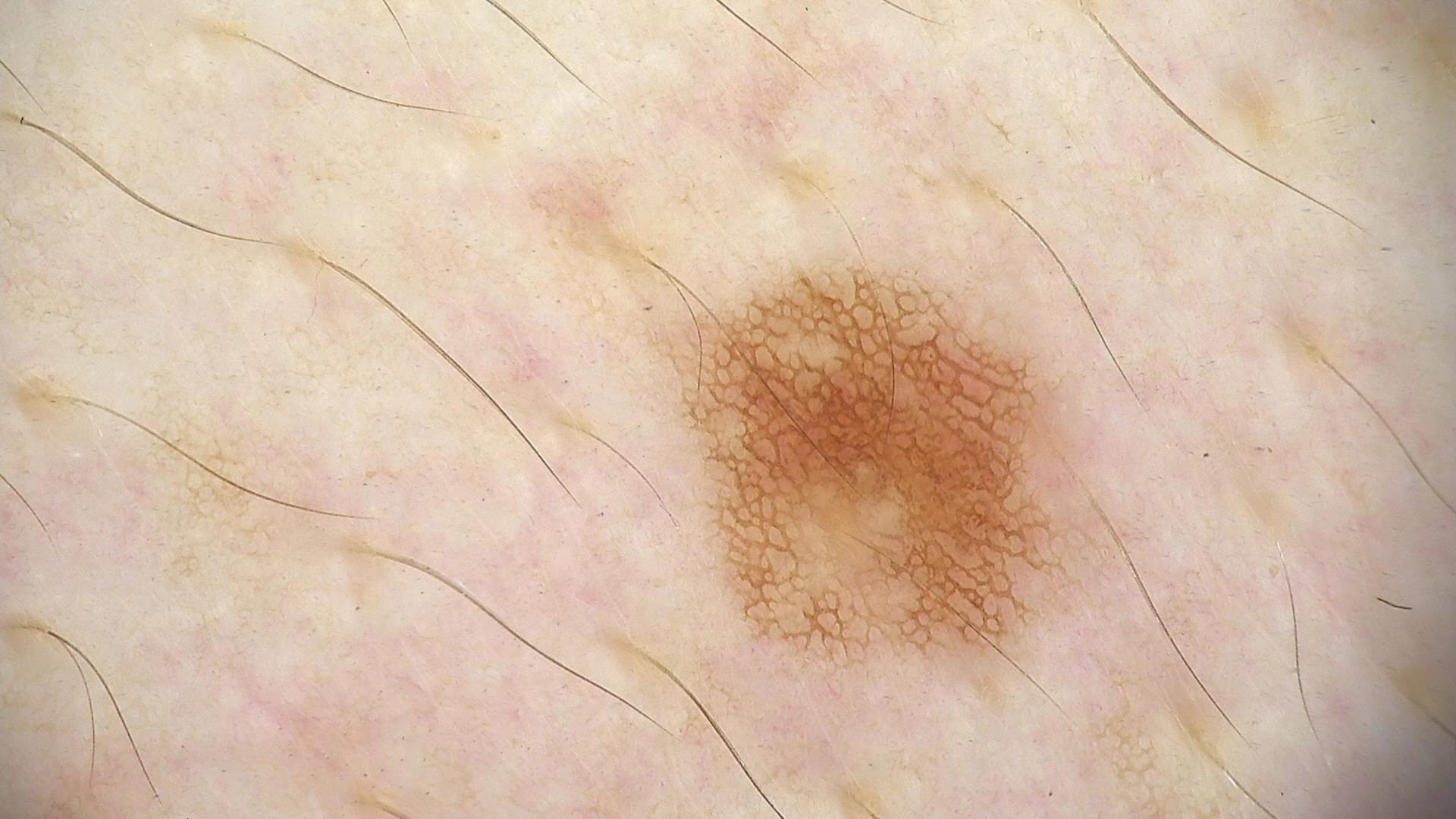A dermoscopic close-up of a skin lesion.
The diagnosis was a dysplastic junctional nevus.